The back of the torso is involved; the contributor is 60–69, male; close-up view — 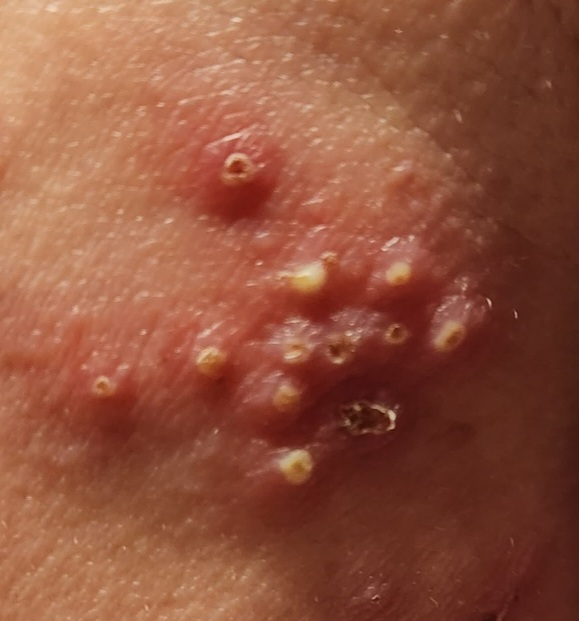Single-reviewer assessment: most consistent with Herpes Simplex.